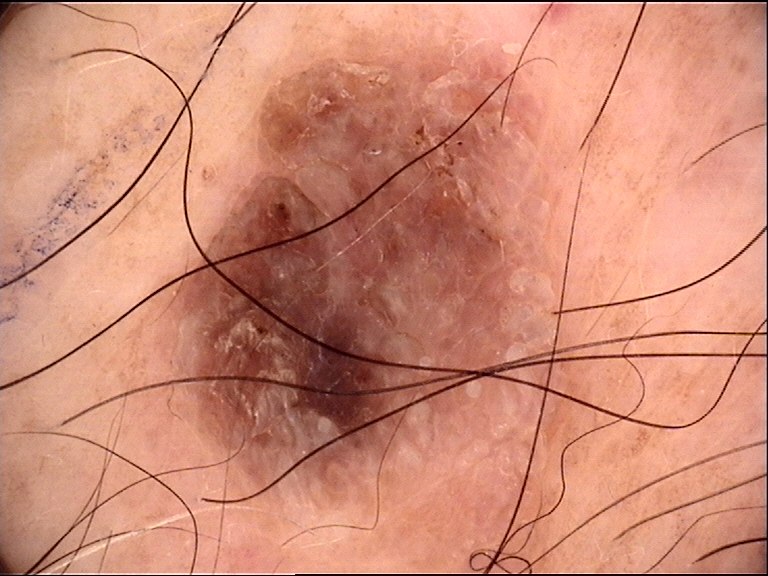The diagnosis was a seborrheic keratosis.